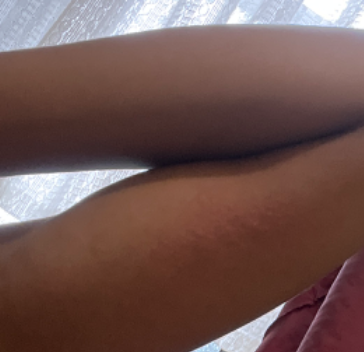Notes:
* assessment: unable to determine
* skin tone: Fitzpatrick skin type V
* lesion texture: raised or bumpy
* self-categorized as: a rash
* associated systemic symptoms: none reported
* view: at a distance
* present for: about one day
* symptoms: bothersome appearance